A skin lesion imaged with a dermatoscope, a female patient approximately 40 years of age.
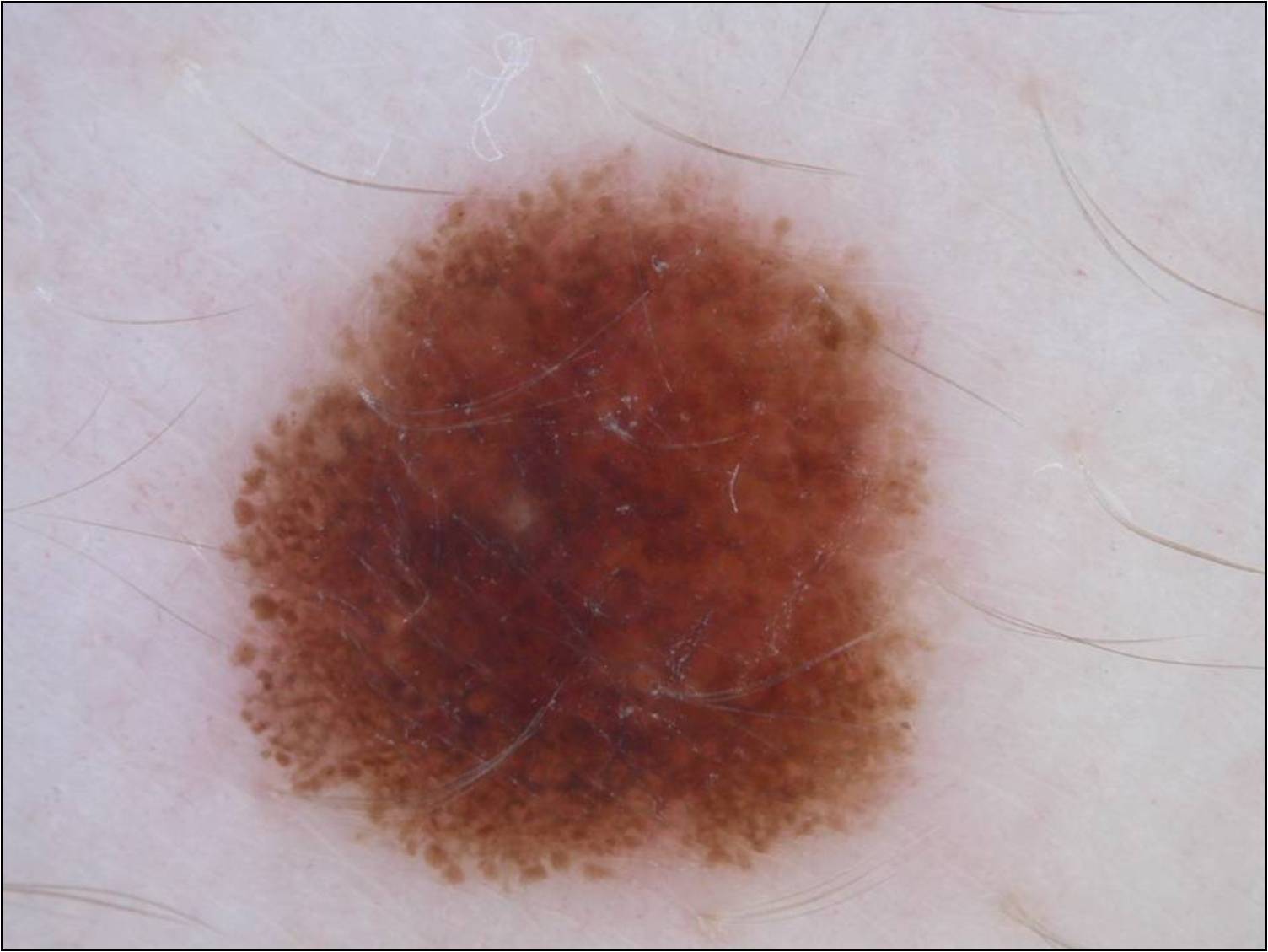Q: Where is the lesion in the image?
A: bbox(219, 153, 927, 886)
Q: How large is the lesion within the image?
A: ~33% of the field
Q: What does dermoscopy show?
A: globules, pigment network, and streaks; absent: milia-like cysts and negative network
Q: What did the assessment conclude?
A: a melanocytic nevus, a benign skin lesion